The photograph is a close-up of the affected area; the patient is a female aged 50–59; the affected area is the top or side of the foot: 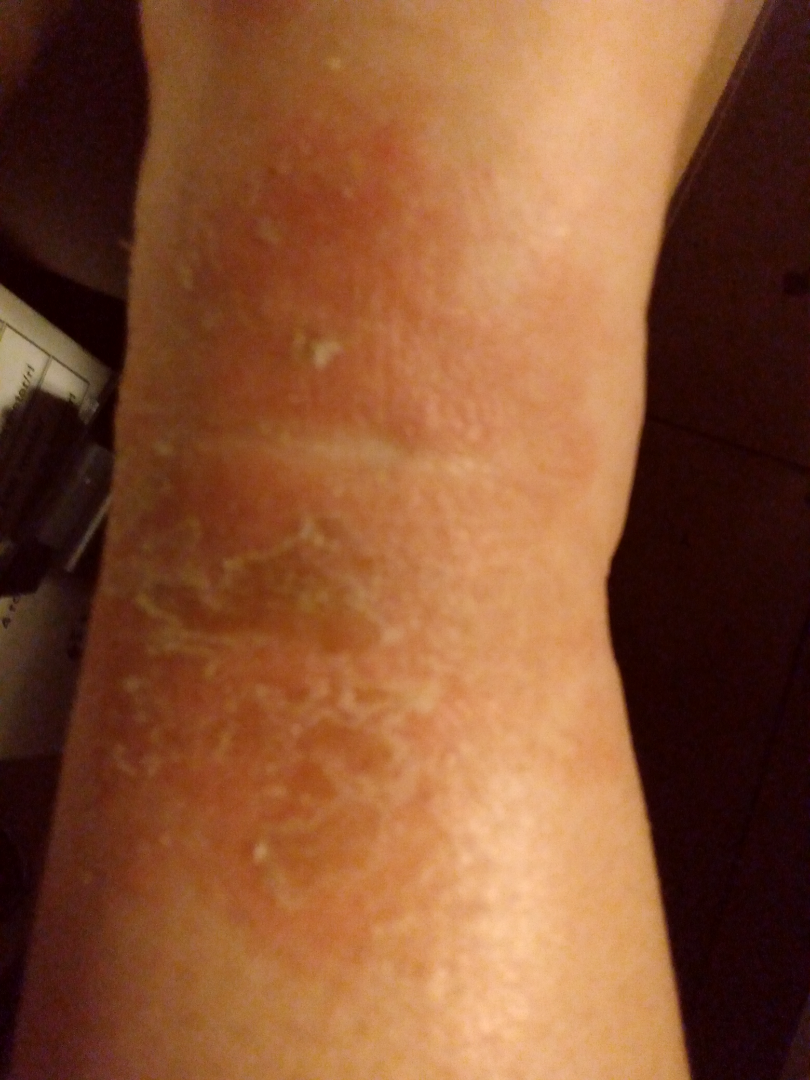{
  "differential": {
    "leading": [
      "Eczema"
    ],
    "unlikely": [
      "Impetigo",
      "Stasis Dermatitis",
      "Ichthyosiform dermatosis"
    ]
  }
}